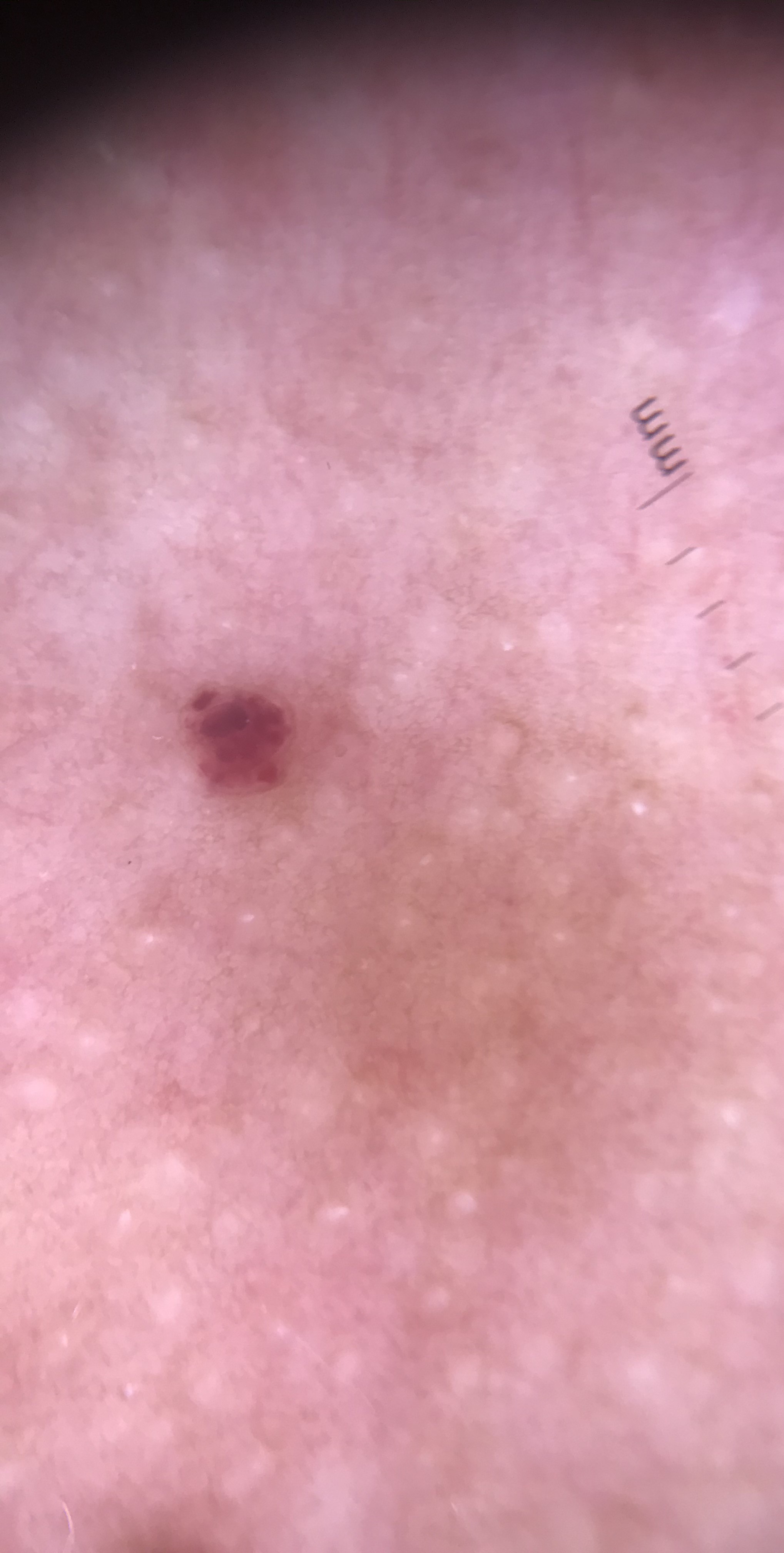Summary: A dermoscopic close-up of a skin lesion. This is a vascular lesion. Conclusion: Labeled as a hemangioma.